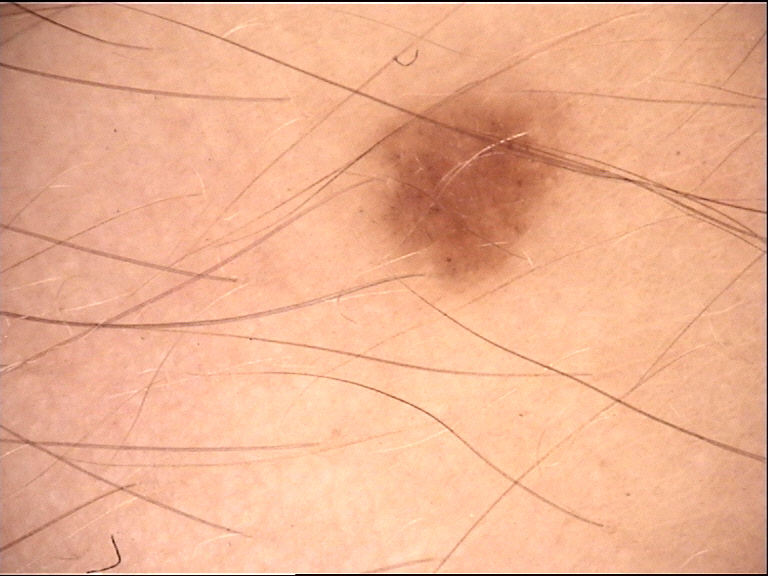Findings: This is a banal lesion. Conclusion: The diagnosis was a junctional nevus.